A dermatoscopic image of a skin lesion.
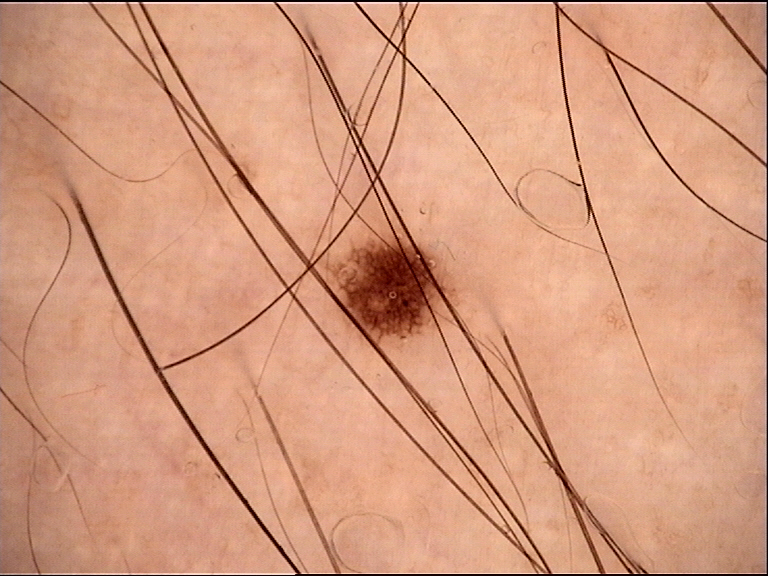Diagnosed as a benign lesion — a dysplastic junctional nevus.